The subject is 50–59, female. The photo was captured at an angle. Located on the front of the torso, back of the hand, back of the torso, arm and palm: 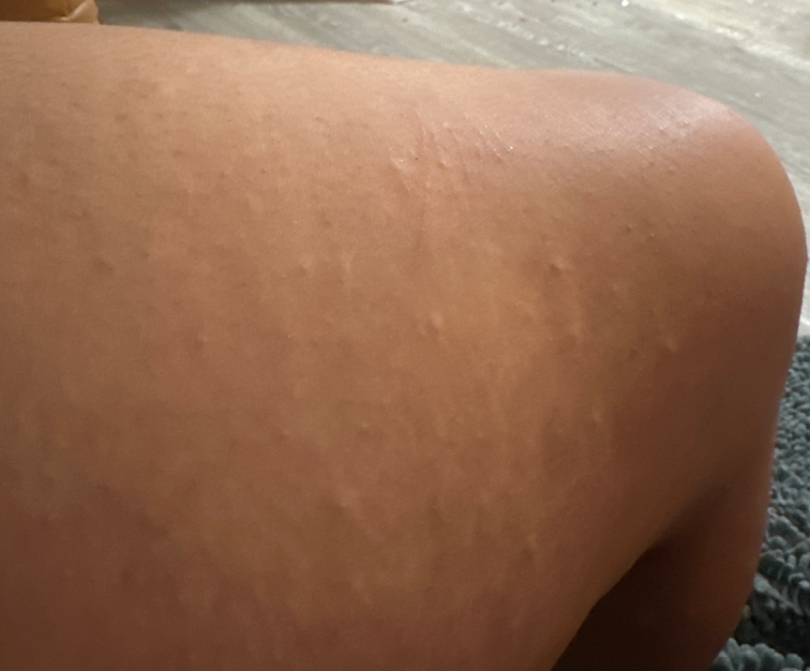Q: What conditions are considered?
A: Allergic Contact Dermatitis and Eczema were considered with similar weight